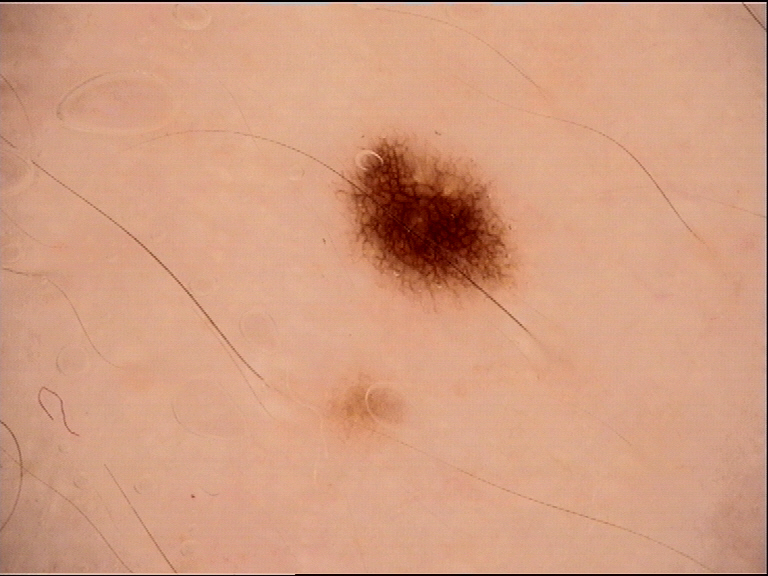Case:
A dermoscopic photograph of a skin lesion.
Conclusion:
The diagnosis was a dysplastic junctional nevus.